No associated systemic symptoms reported; the photograph was taken at an angle; texture is reported as flat and raised or bumpy; present for about one day.
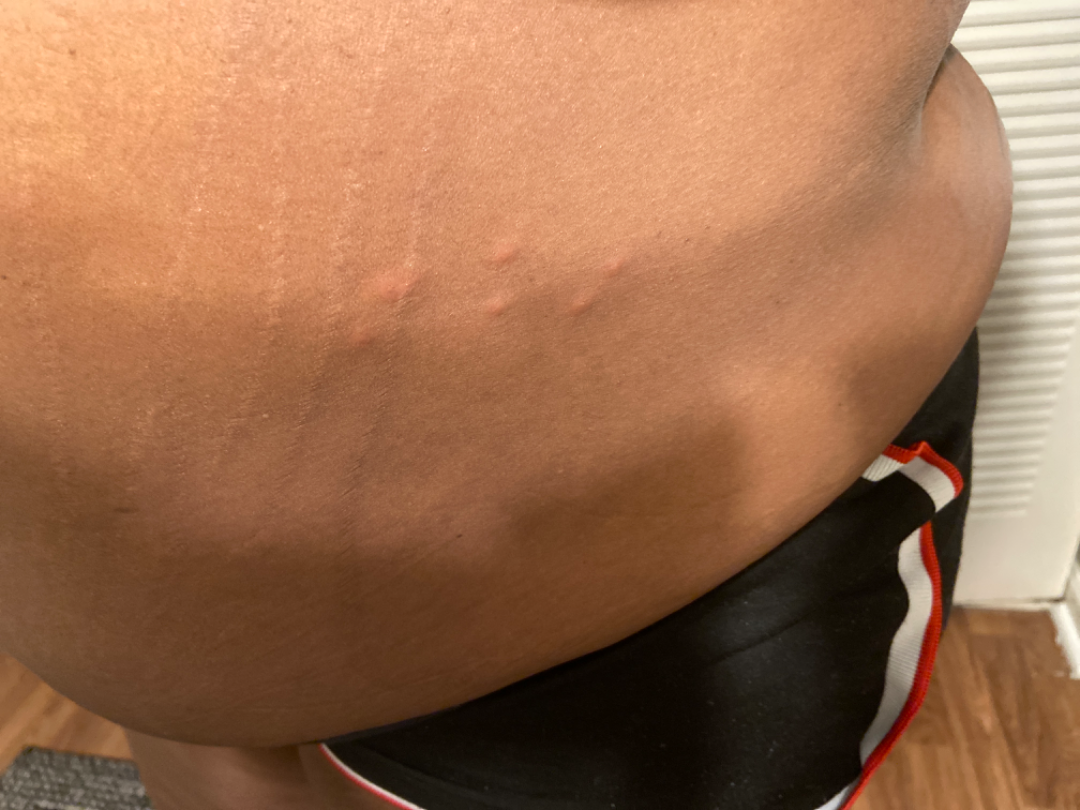| key | value |
|---|---|
| assessment | not assessable |